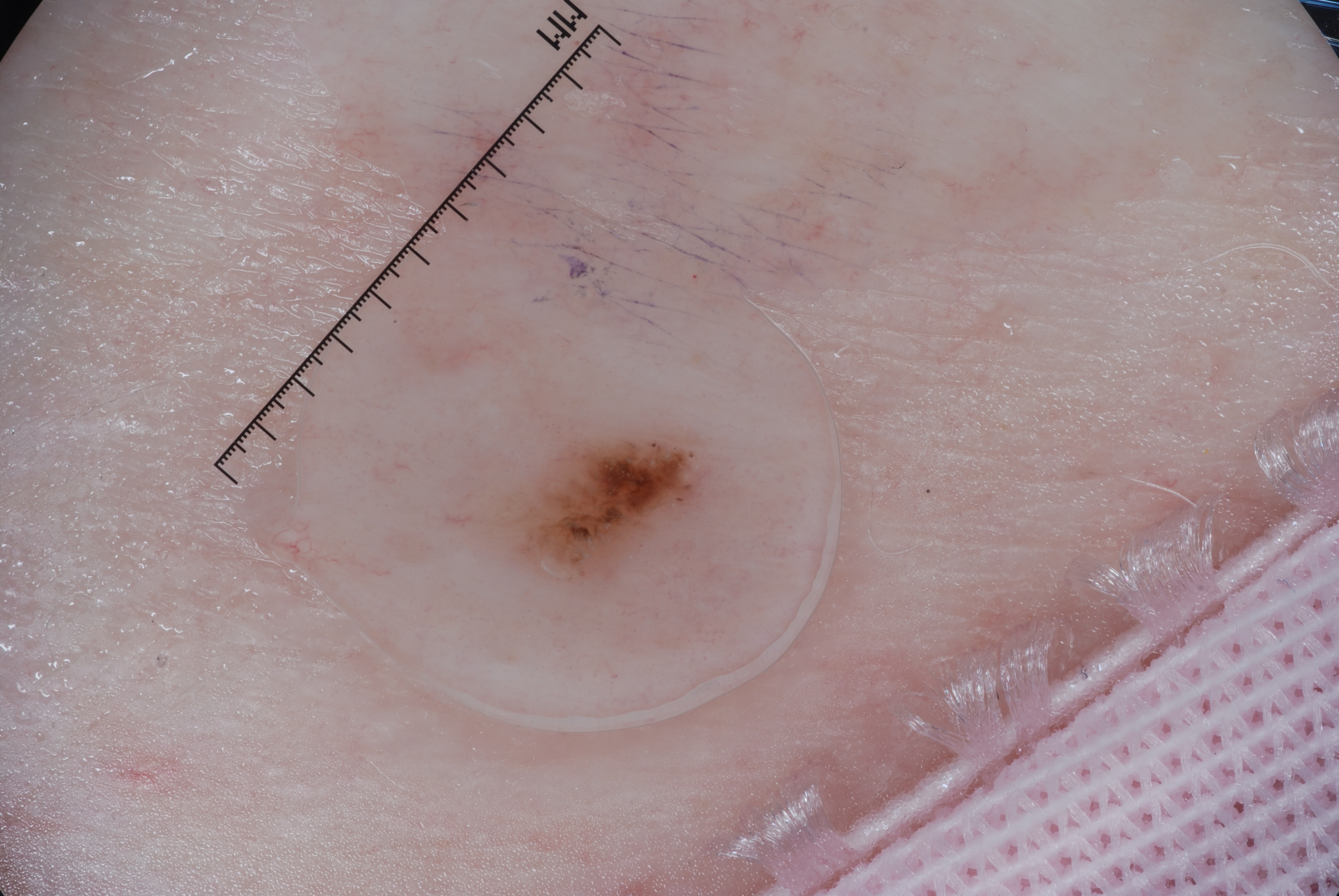Case summary:
A female subject, roughly 65 years of age. A dermoscopy image of a single skin lesion. Dermoscopically, the lesion shows milia-like cysts. As (left, top, right, bottom), lesion location: 505 438 701 581.
Conclusion:
The diagnostic assessment was a seborrheic keratosis, a benign lesion.